The photograph was taken at an angle — 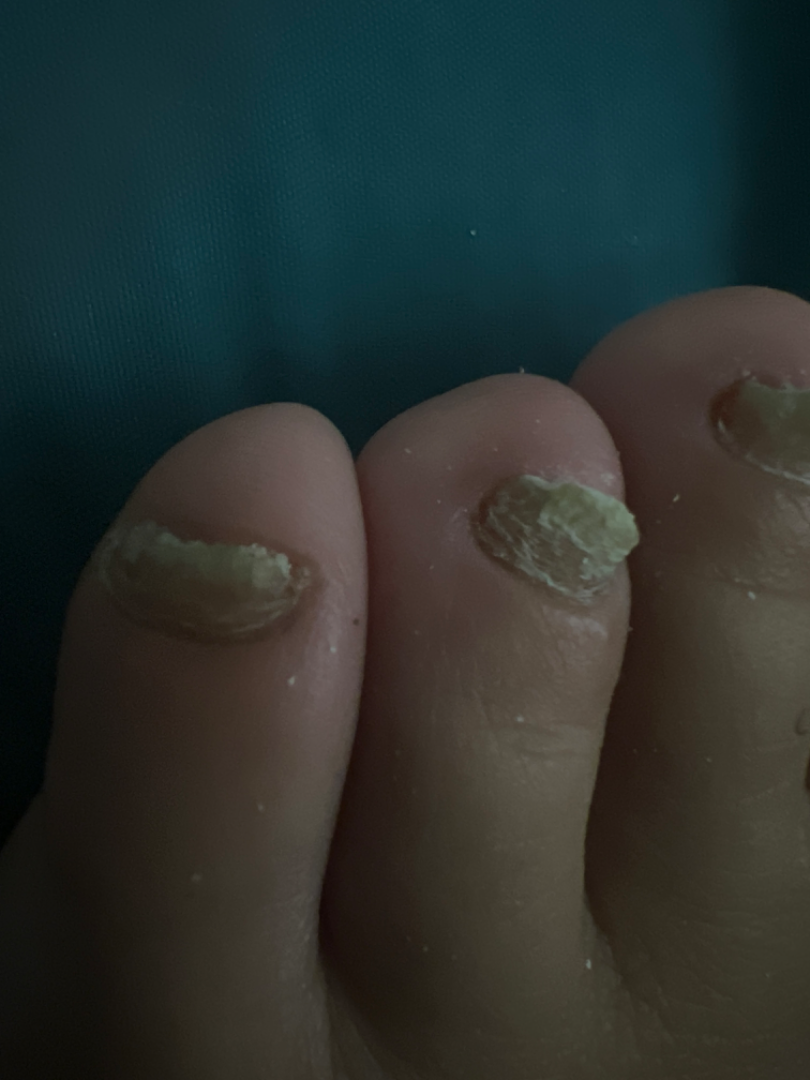On remote dermatologist review: Onychomycosis (54%); Onychodystrophy (23%); Psoriasis (23%).